A skin lesion imaged with a dermatoscope.
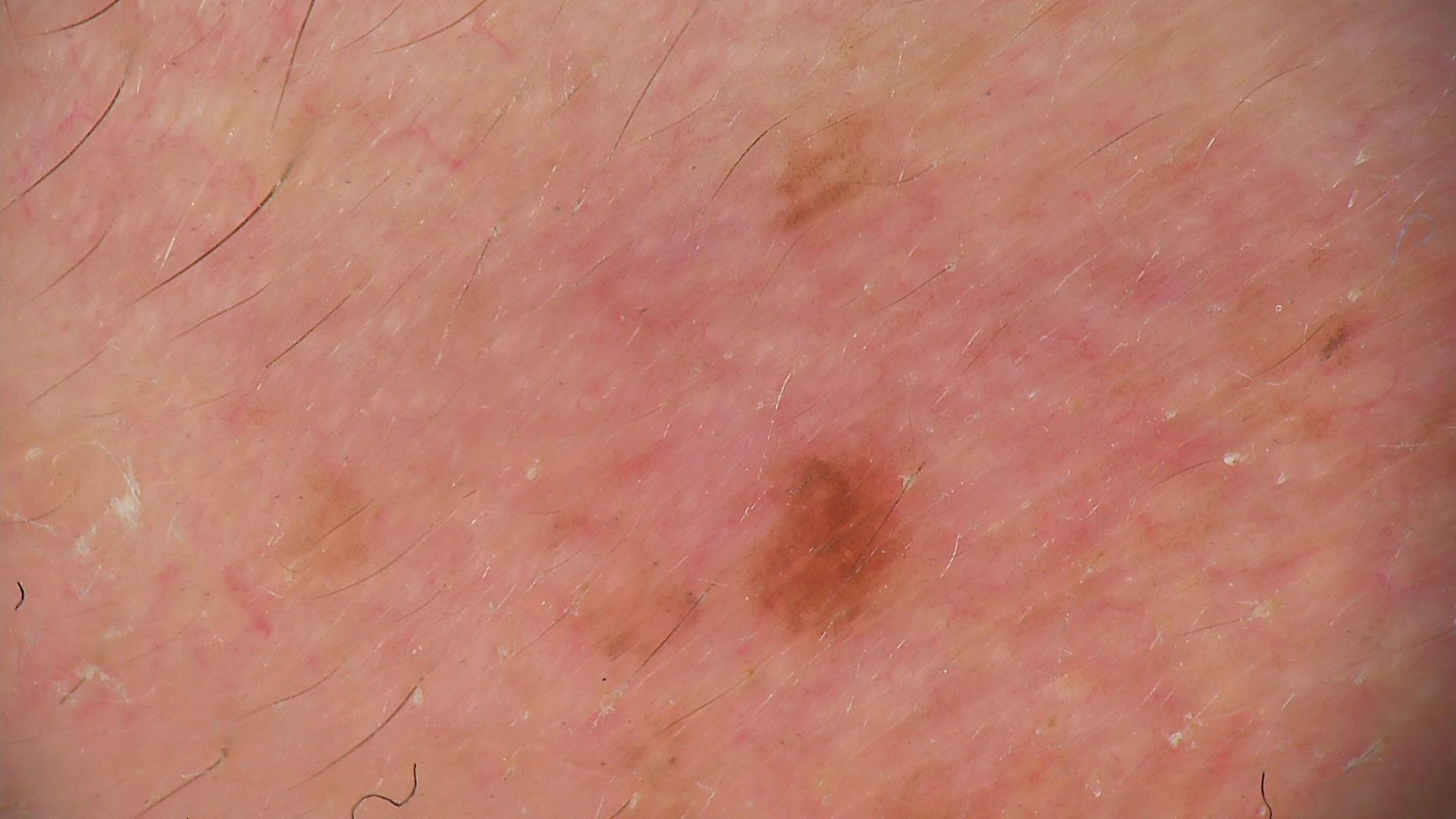Q: How is the lesion classified?
A: keratinocytic
Q: What is the diagnosis?
A: seborrheic keratosis (expert consensus)